The photograph was taken at an angle.
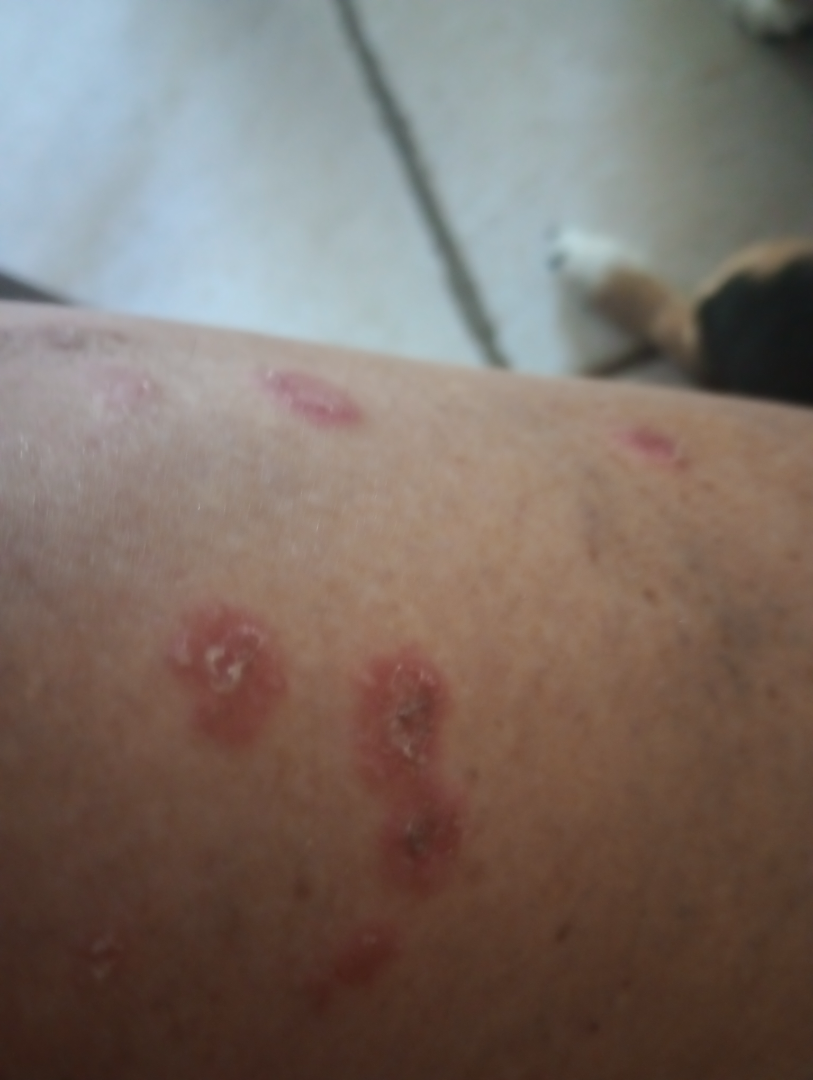A single dermatologist reviewed the case: favoring Pityriasis rosea; an alternative is Eczema; a more distant consideration is Erythema multiforme.